Recorded as FST II. A male patient 83 years of age. The chart notes prior malignancy (patient or family) and pesticide exposure — 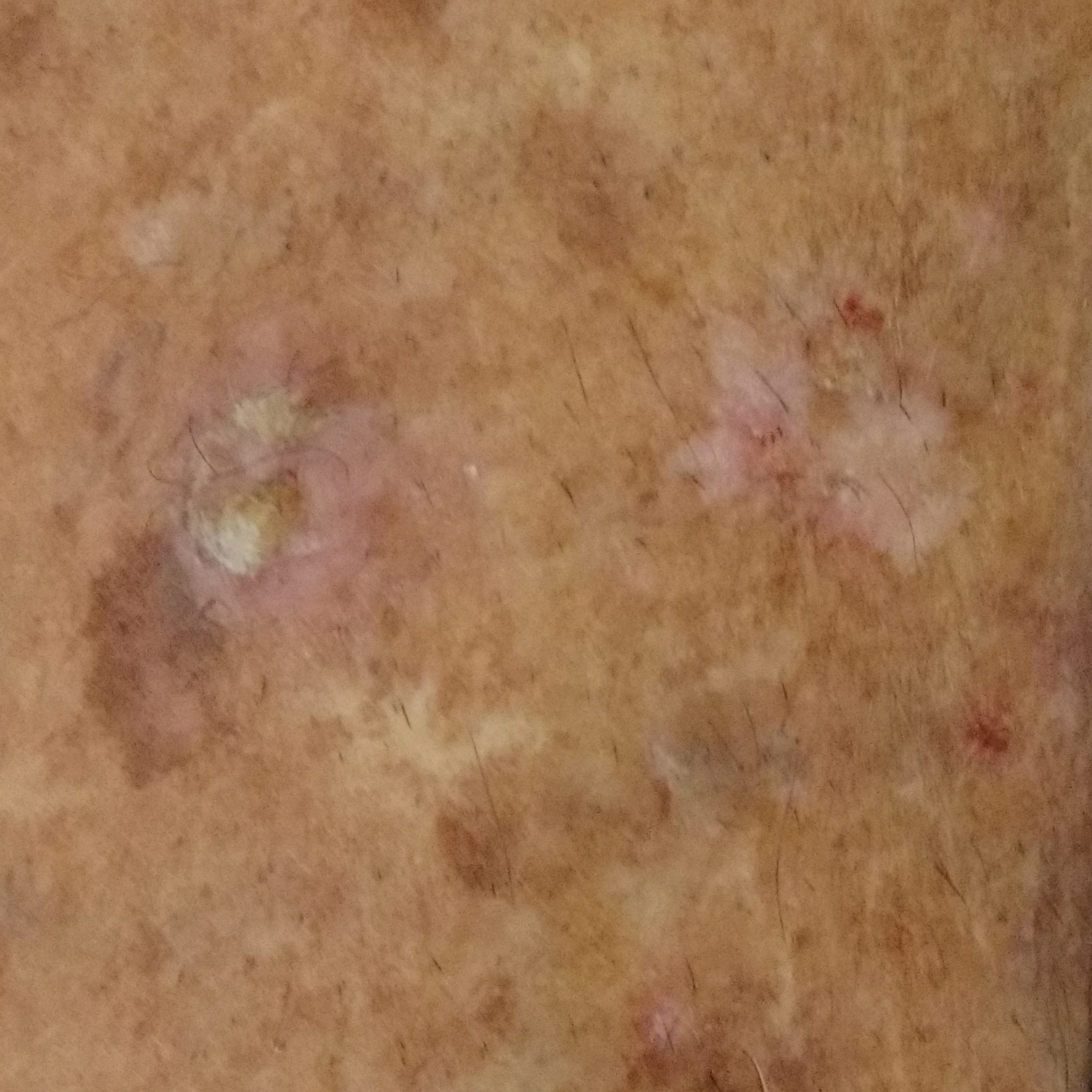{
  "lesion_location": "a forearm",
  "lesion_size": {
    "diameter_1_mm": 35.0,
    "diameter_2_mm": 15.0
  },
  "symptoms": {
    "present": [
      "itching"
    ],
    "absent": [
      "elevation"
    ]
  },
  "diagnosis": {
    "name": "actinic keratosis",
    "code": "ACK",
    "malignancy": "indeterminate",
    "confirmation": "histopathology"
  }
}